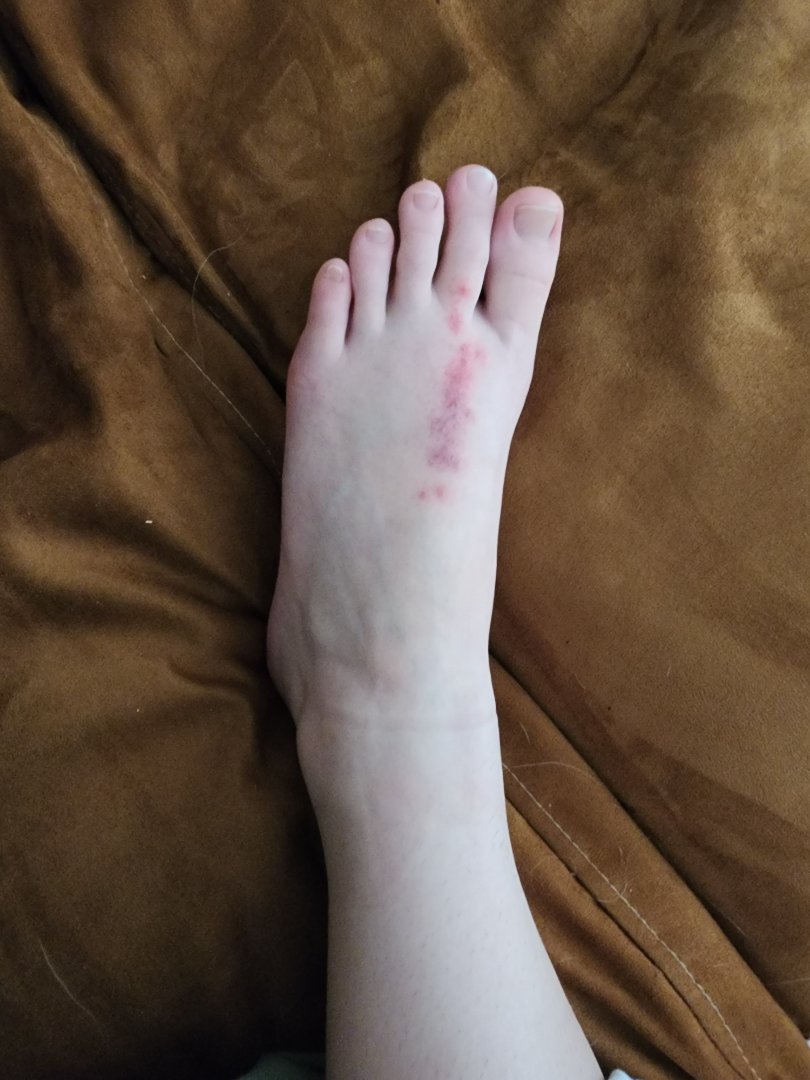anatomic site: top or side of the foot
shot type: at a distance
contributor: female, age 18–29
differential: the leading impression is Allergic Contact Dermatitis; possibly Insect Bite; less probable is Herpes Zoster; a remote consideration is Cutaneous larva migrans